A female patient approximately 30 years of age; the chart documents a first-degree relative with melanoma; a contact-polarized dermoscopy image of a skin lesion: 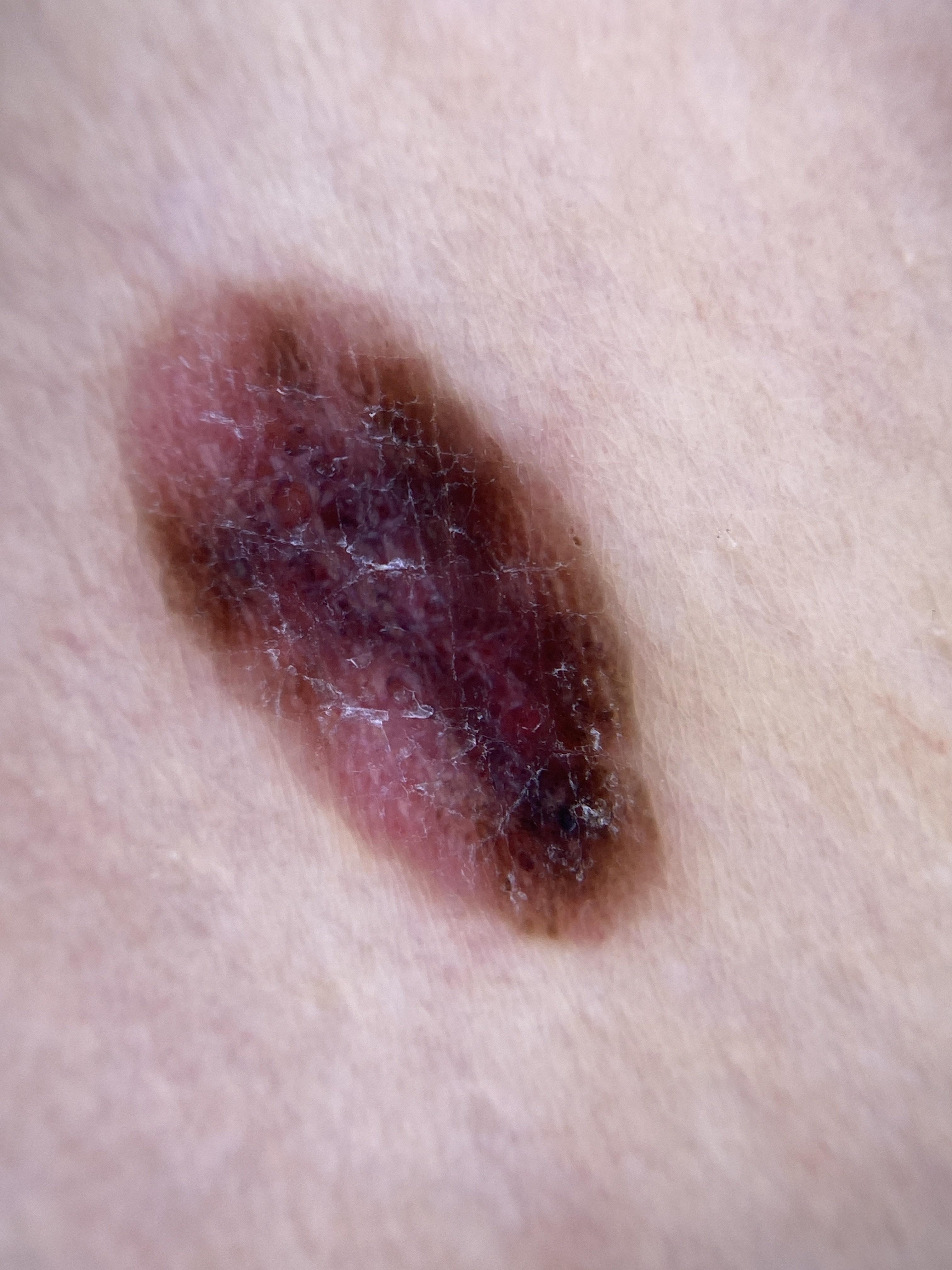Located on a lower extremity.
Histopathological examination showed a nevus.